A skin lesion imaged with a dermatoscope.
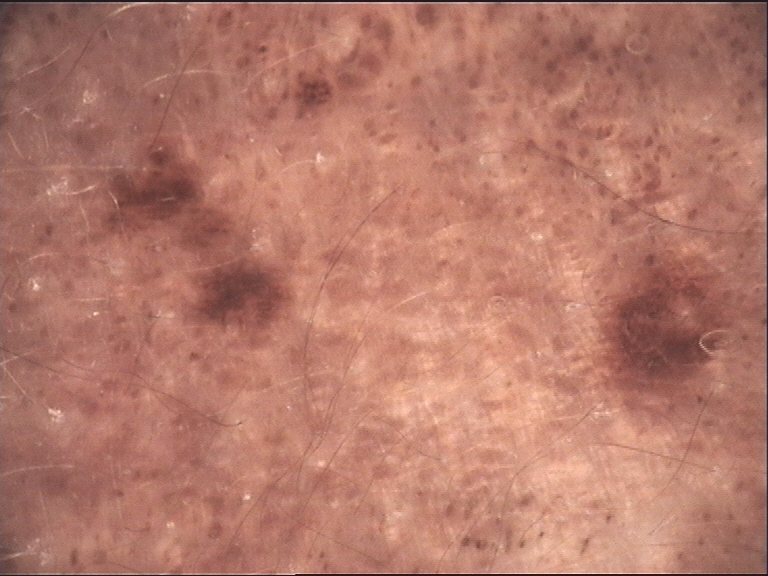The diagnostic label was a banal lesion — a congenital compound nevus.